A dermoscopic image of a skin lesion.
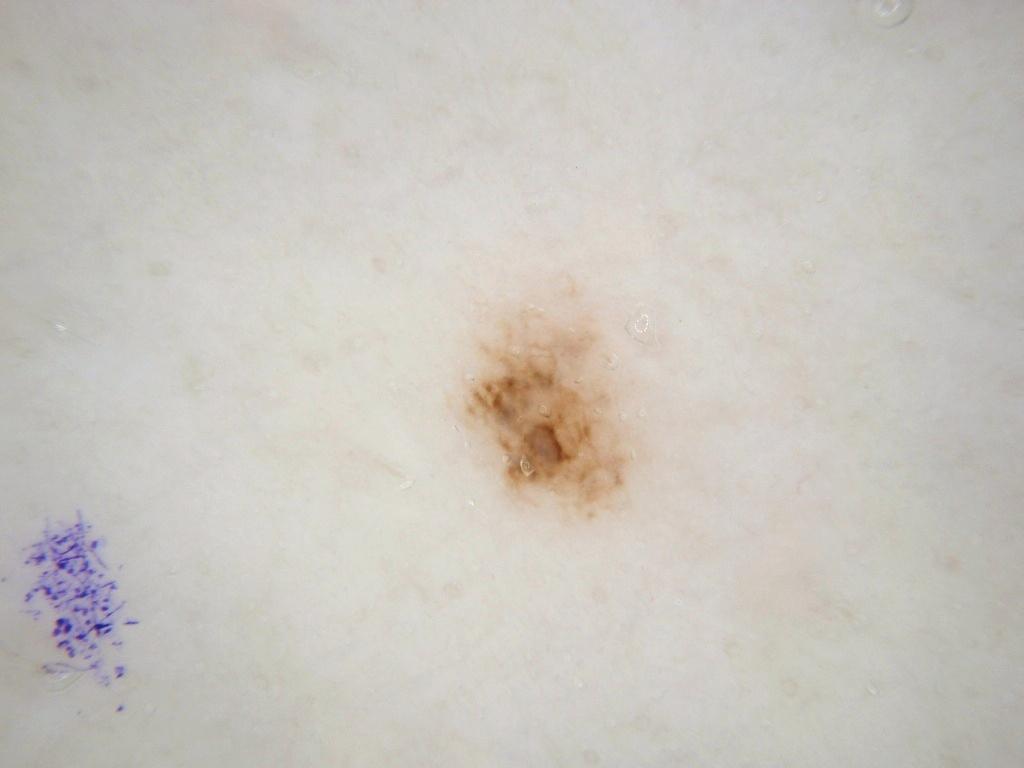dermoscopic features assessed but absent = globules, milia-like cysts, pigment network, negative network, and streaks; location = 462, 309, 639, 519; impression = a melanocytic nevus, a benign lesion.